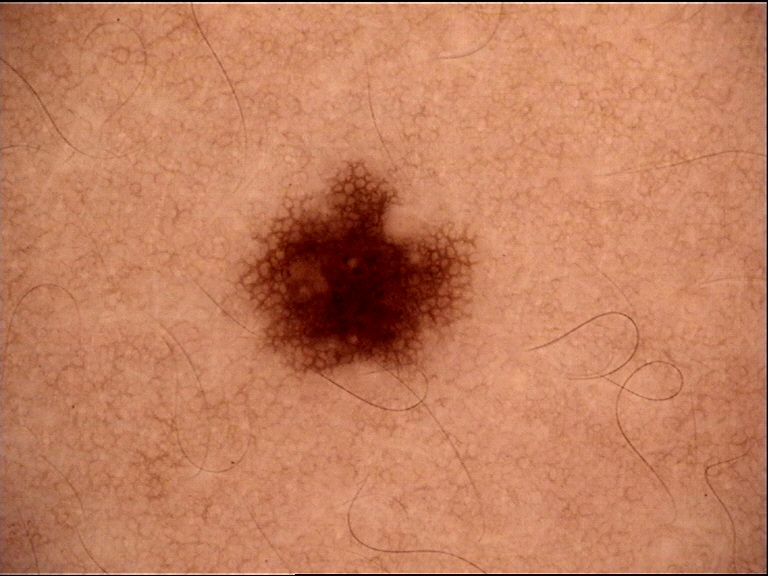Case:
- modality: dermoscopy
- assessment: dysplastic junctional nevus (expert consensus)